The affected area is the arm · the photograph was taken at a distance:
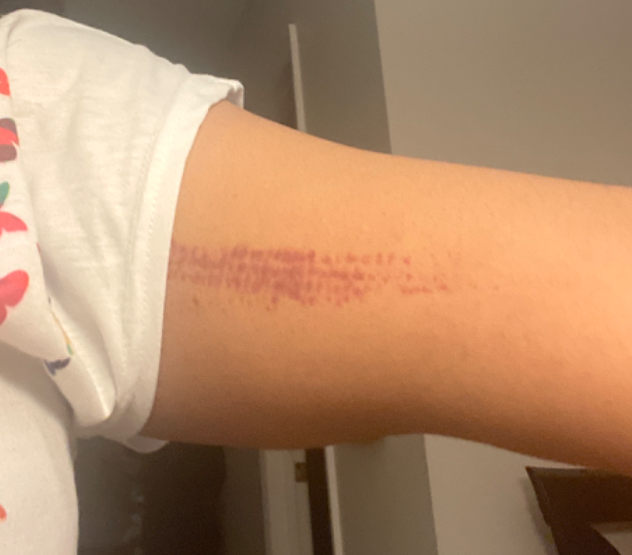A single dermatologist reviewed the case: most consistent with ecchymoses.